A clinical photograph of a skin lesion; the patient says their skin reddens with sun exposure; the patient describes having a moderate number of moles.
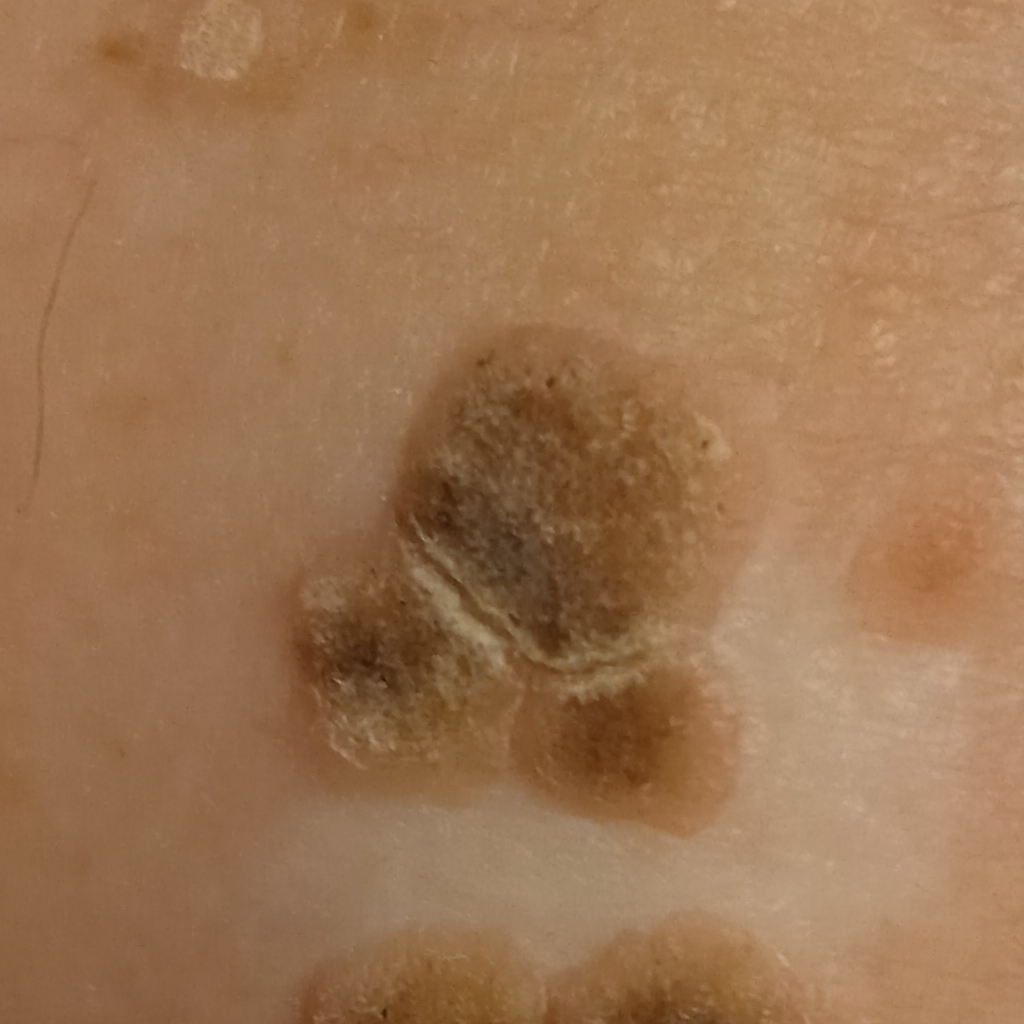Q: What is the anatomic site?
A: the back
Q: How large is the lesion?
A: 14.2 mm
Q: What was the diagnosis?
A: seborrheic keratosis (dermatologist consensus)